A dermoscopy image of a single skin lesion · a female patient aged approximately 85 or older: 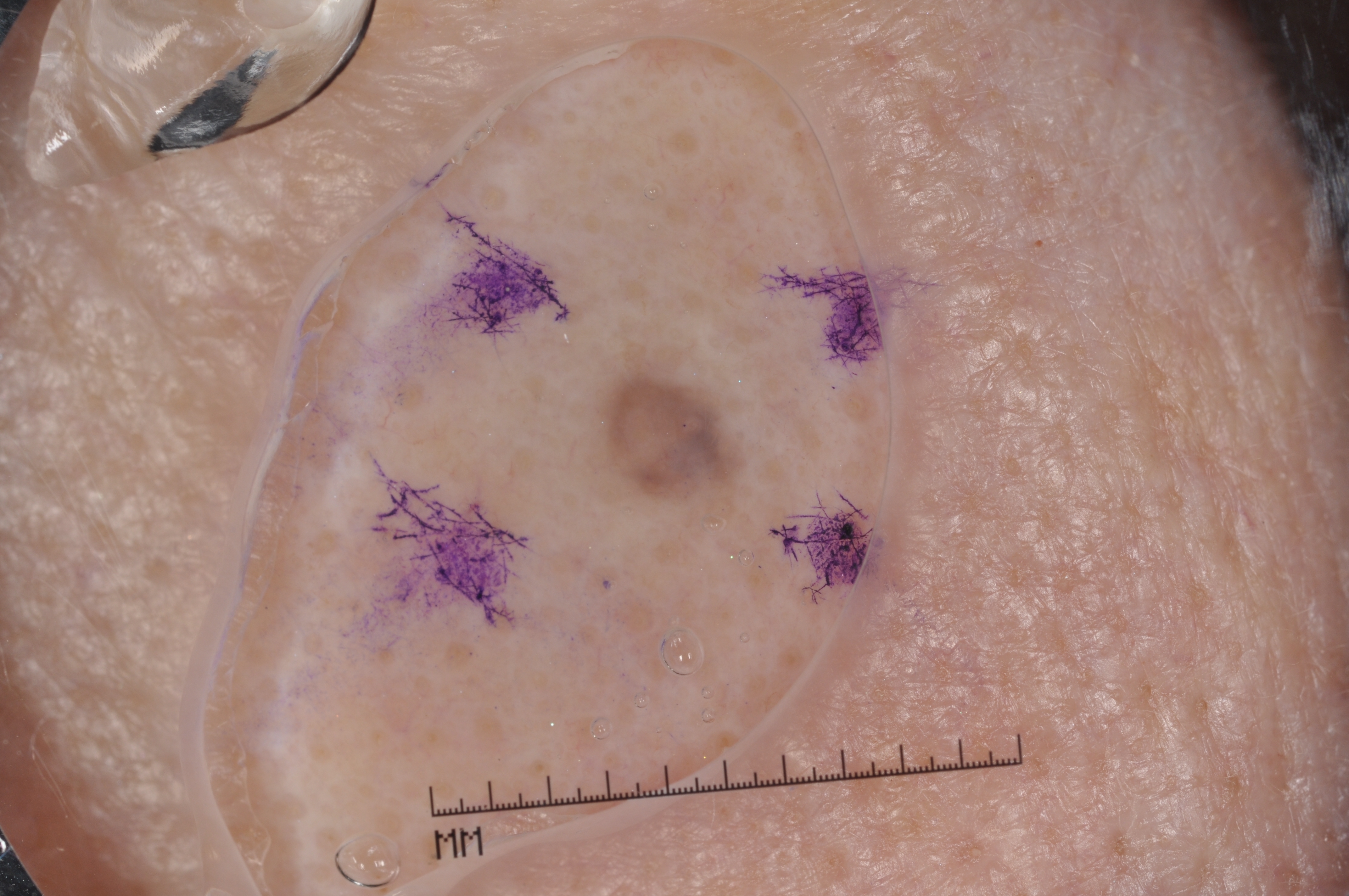Case summary:
The lesion takes up about 1% of the image. In (x1, y1, x2, y2) order, the lesion is bounded by 586 342 745 519. On dermoscopy, the lesion shows no milia-like cysts, negative network, pigment network, or streaks.
Assessment:
Diagnosed as a melanocytic nevus, a benign lesion.